A patient in their 60s — 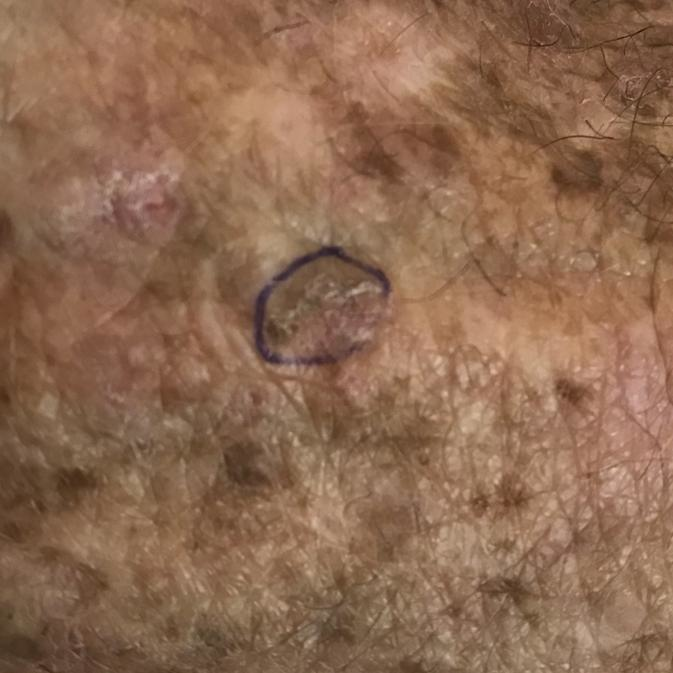The lesion was found on a hand.
The patient describes that the lesion itches and has grown.
Consistent with an actinic keratosis.